The lesion involves the back of the torso, arm, head or neck, leg and front of the torso; the patient is a female aged 40–49; the photo was captured at an angle — 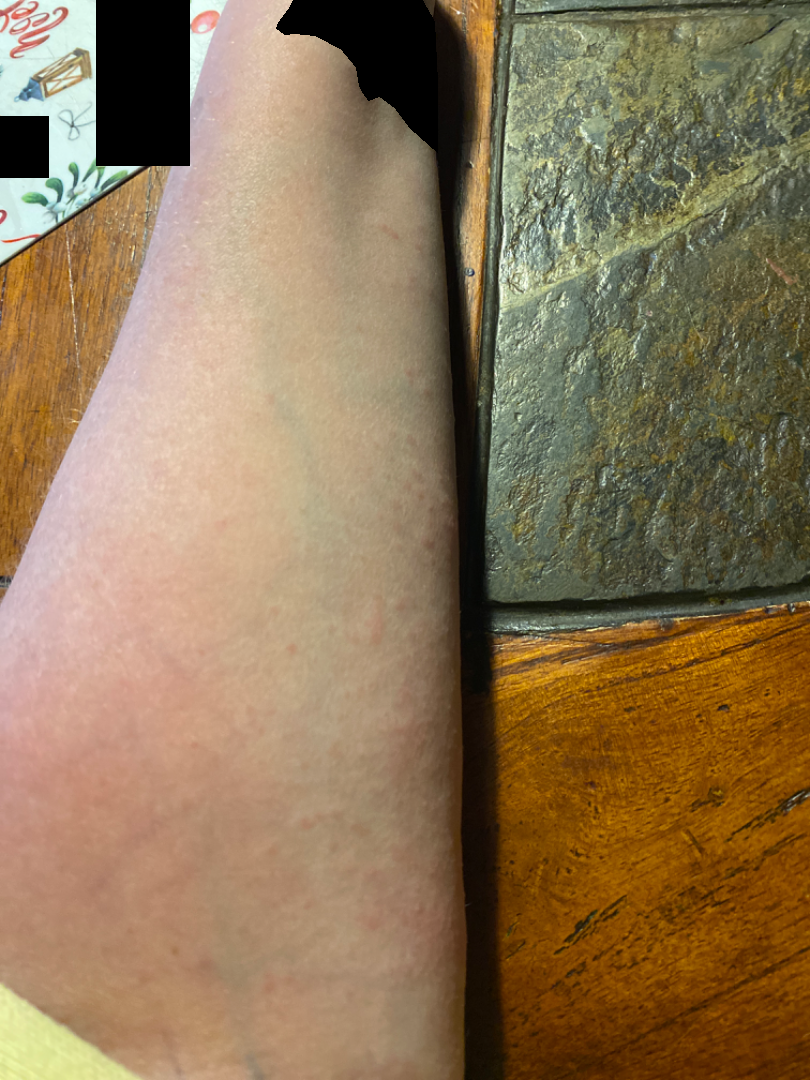Notes:
* diagnostic considerations: Allergic Contact Dermatitis (leading); Eczema (considered); Viral Exanthem (unlikely); Hypersensitivity (unlikely)